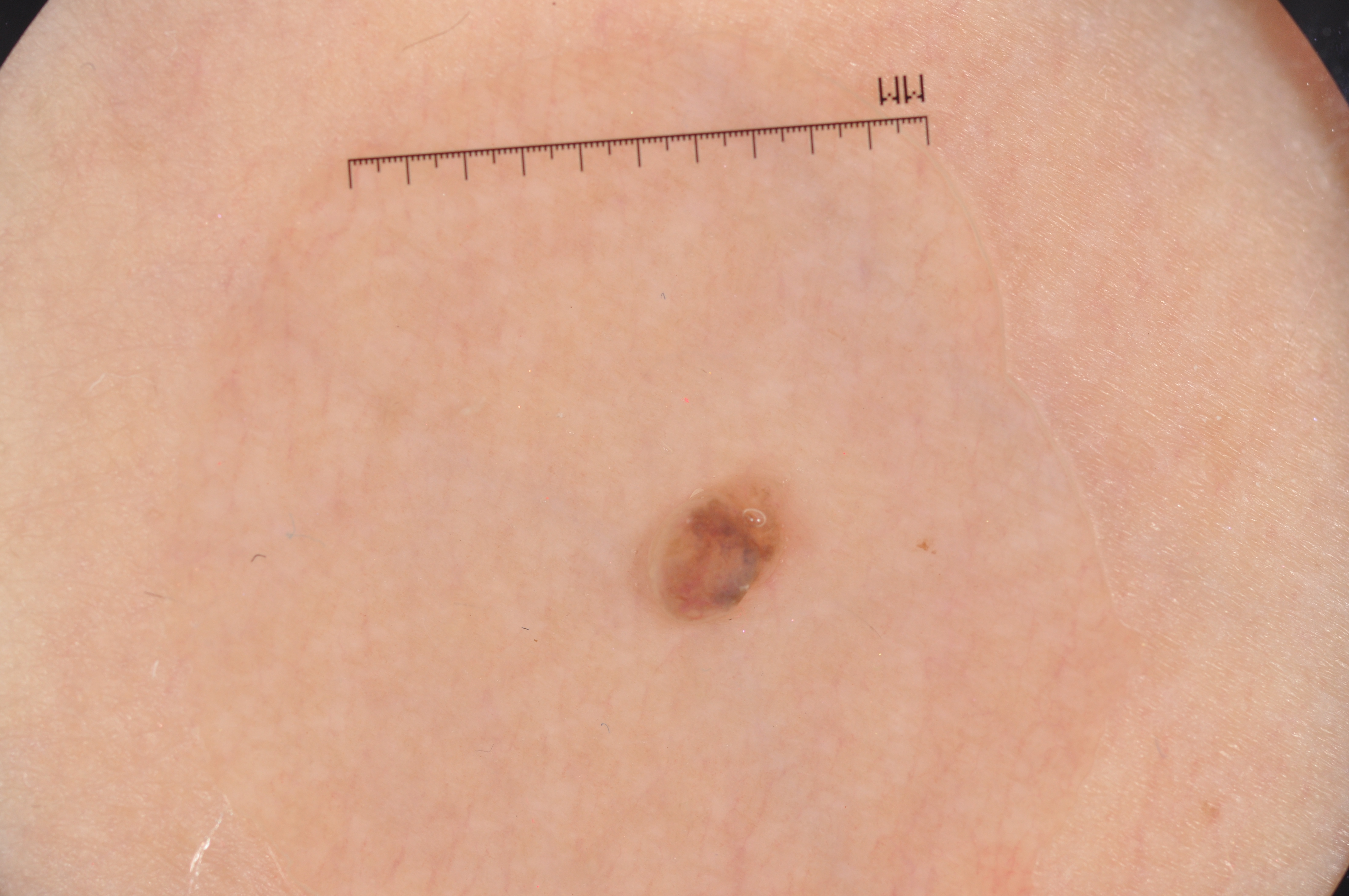A skin lesion imaged with a dermatoscope.
A female subject, in their 40s.
The lesion takes up about 2% of the image.
In (x1, y1, x2, y2) order, the lesion is located at bbox=[636, 468, 798, 624].
The dermoscopic pattern shows milia-like cysts, with no negative network, streaks, or pigment network.
Clinically diagnosed as a melanocytic nevus.